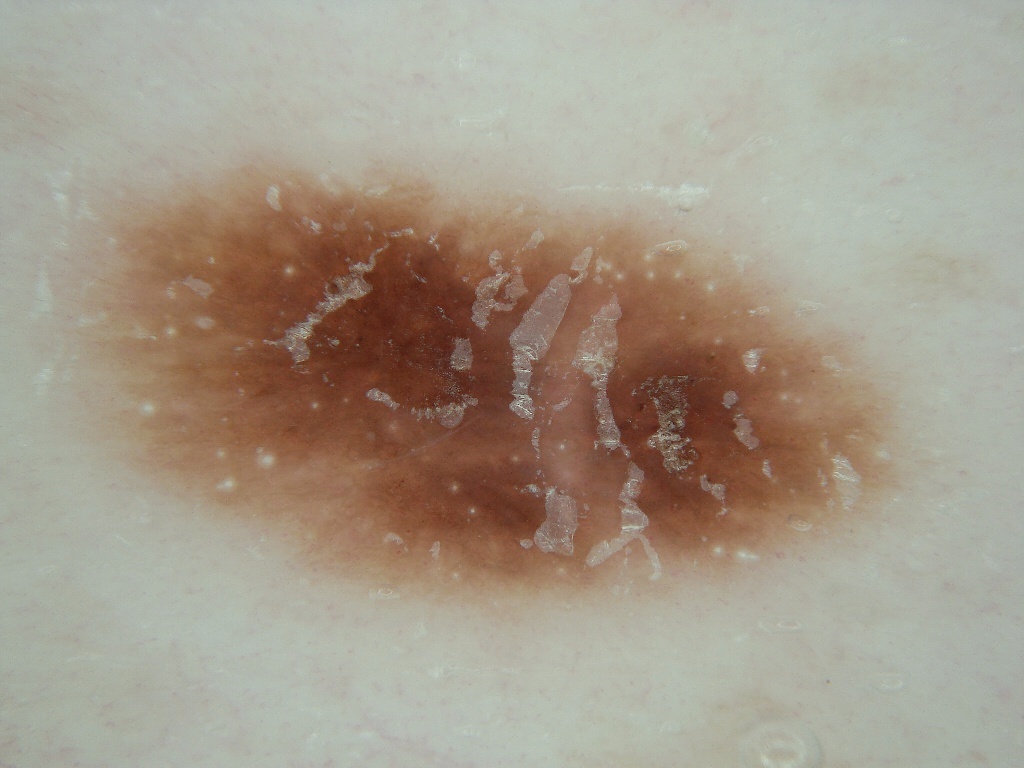Findings:
A dermoscopic close-up of a skin lesion. The lesion takes up about 34% of the image. The dermoscopic pattern shows no globules or streaks. In (x1, y1, x2, y2) order, the lesion is bounded by (62, 158, 898, 612).
Assessment:
Consistent with a benign skin lesion.